A female patient, aged approximately 10 · this is a dermoscopic photograph of a skin lesion:
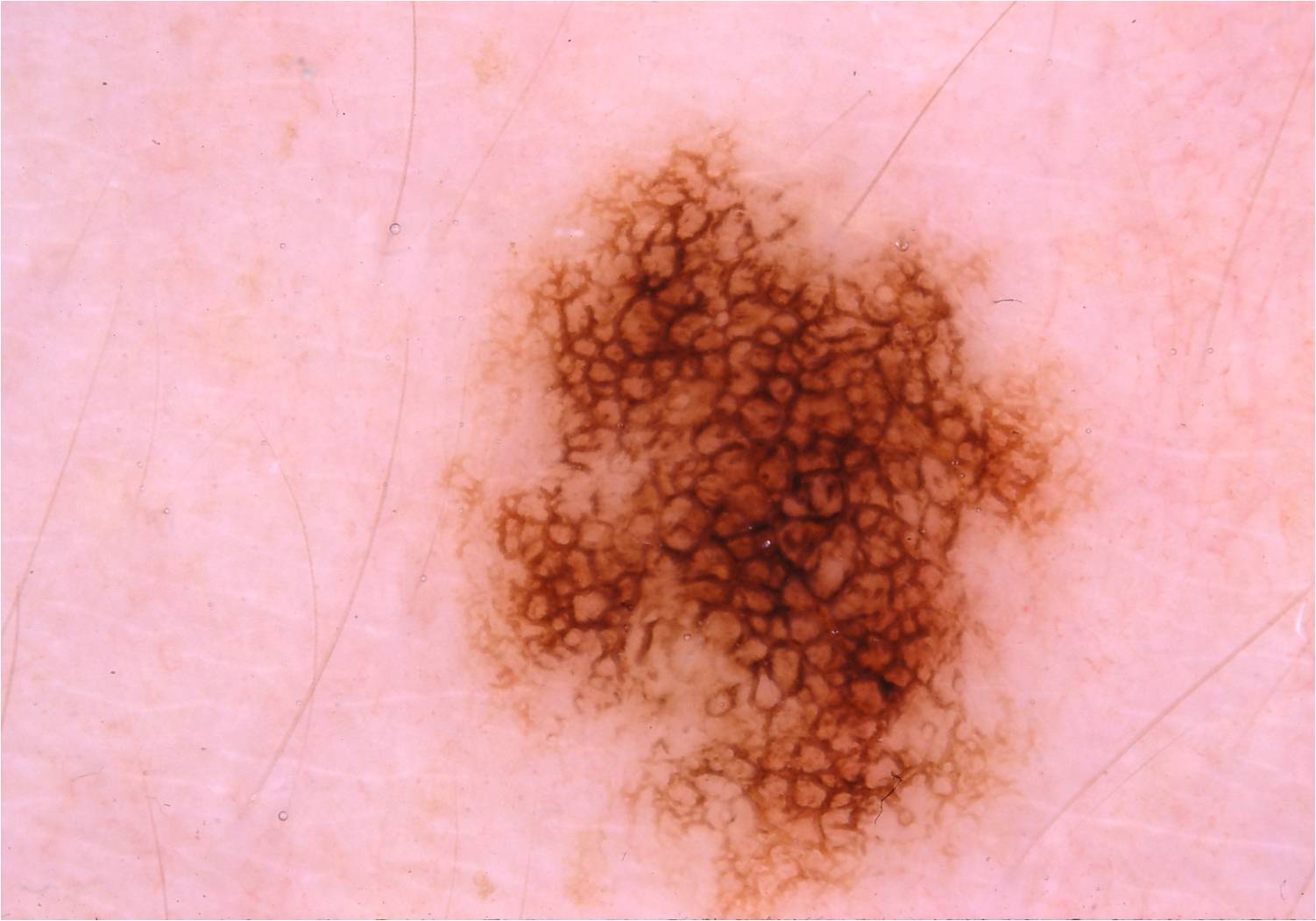Image and clinical context: As (left, top, right, bottom), the lesion occupies the region 440/126/1095/917. Dermoscopic examination shows pigment network. Conclusion: Diagnosed as a melanocytic nevus.